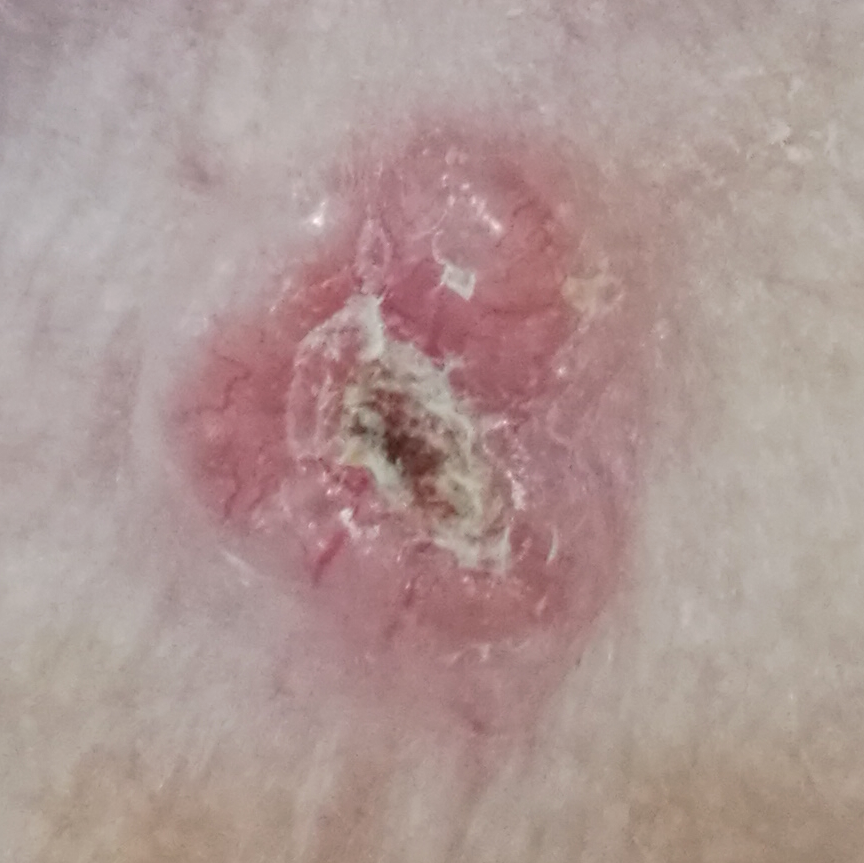Confirmed on histopathology as a basal cell carcinoma.